A dermoscopic photograph of a skin lesion: 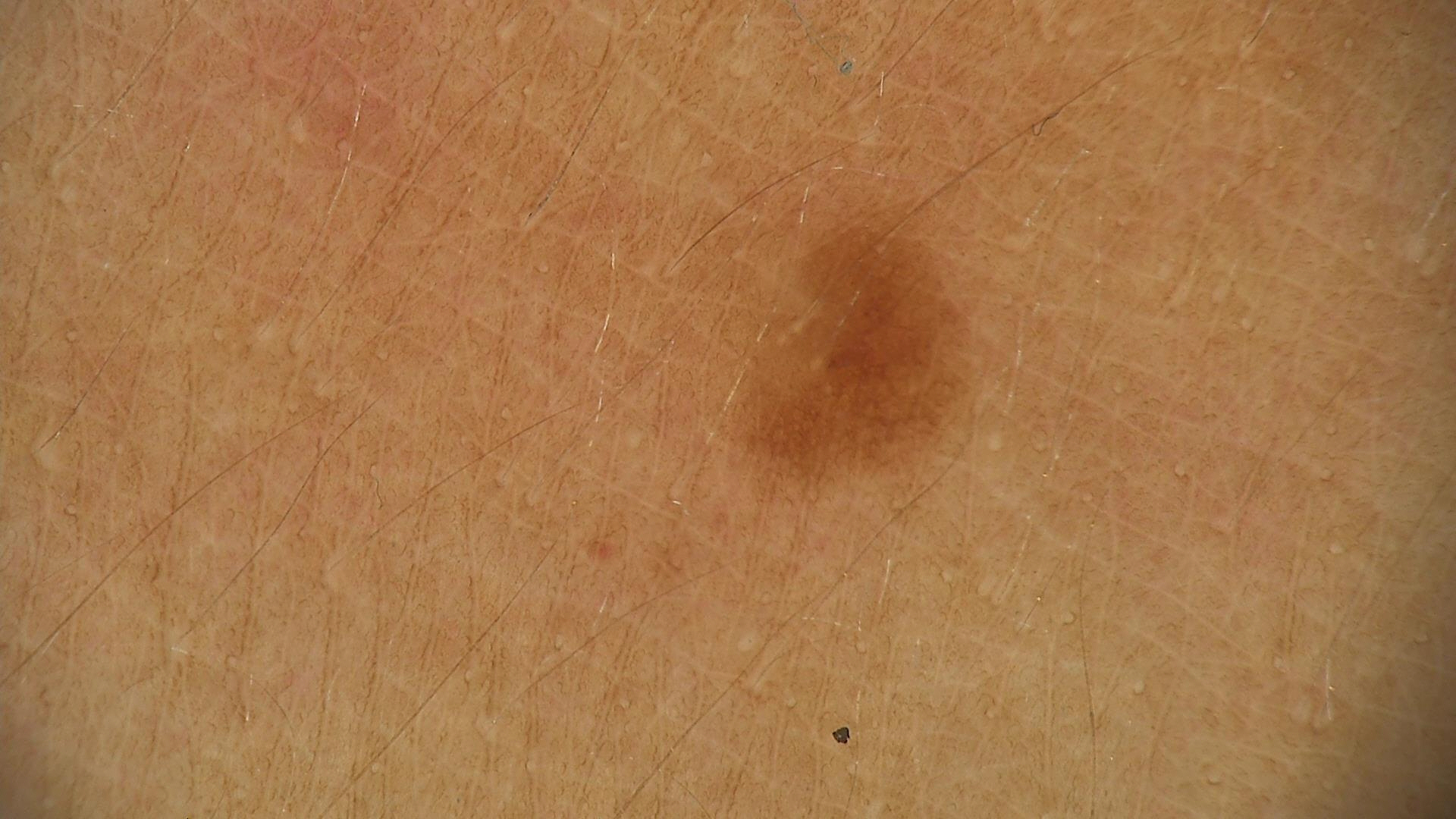<dermoscopy>
<diagnosis>
<name>junctional nevus</name>
<code>jb</code>
<malignancy>benign</malignancy>
<super_class>melanocytic</super_class>
<confirmation>expert consensus</confirmation>
</diagnosis>
</dermoscopy>